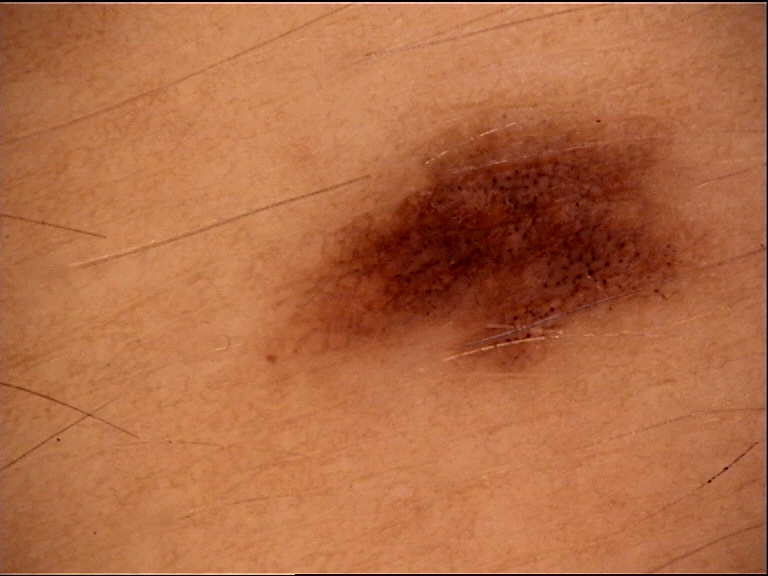Labeled as a junctional nevus.